A dermoscopic close-up of a skin lesion, the patient is a female about 70 years old: 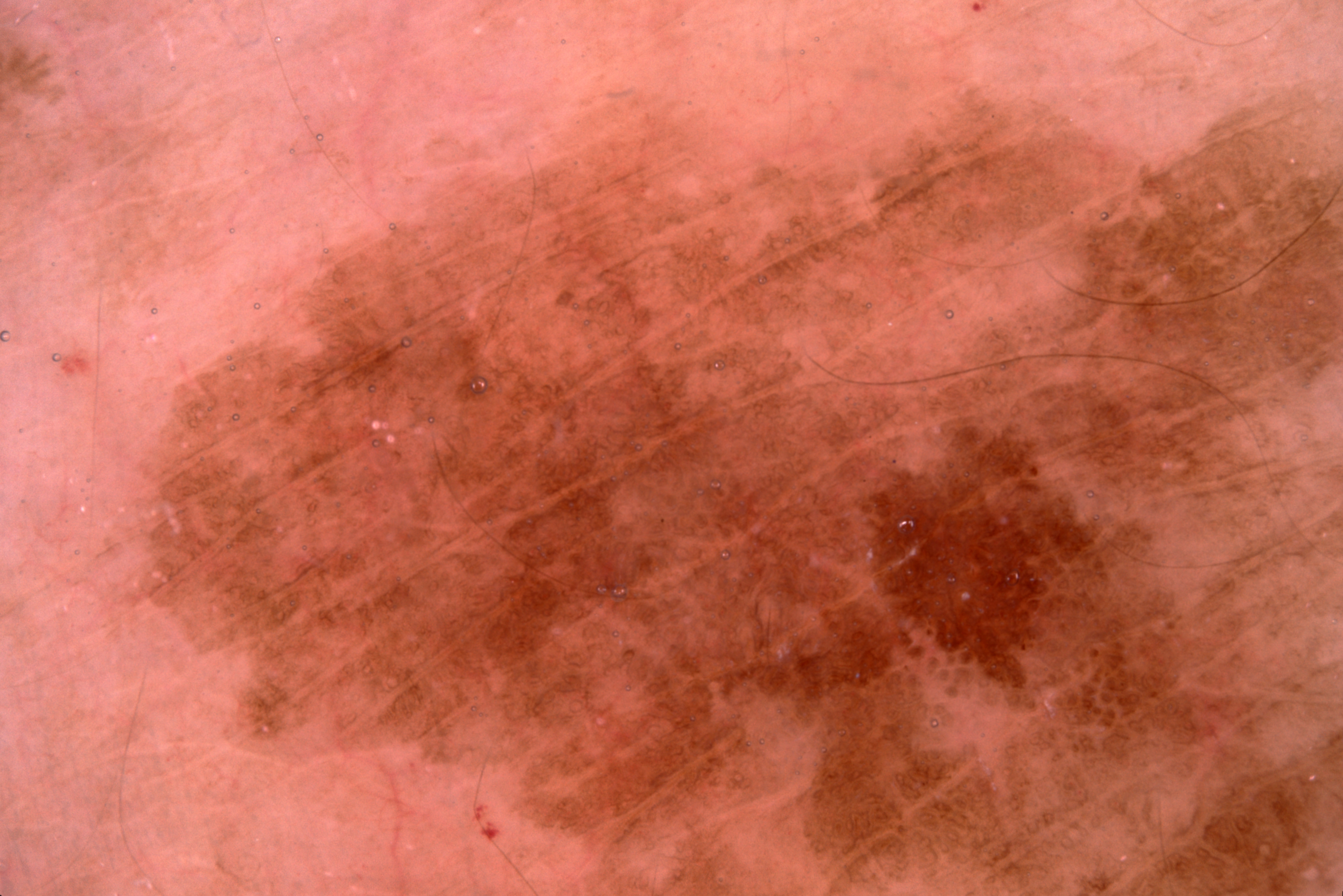lesion_location:
  bbox_xyxy:
    - 137
    - 105
    - 1342
    - 895
dermoscopic_features:
  present:
    - milia-like cysts
    - pigment network
    - negative network
  absent:
    - streaks
diagnosis:
  name: seborrheic keratosis
  malignancy: benign
  lineage: keratinocytic
  provenance: clinical